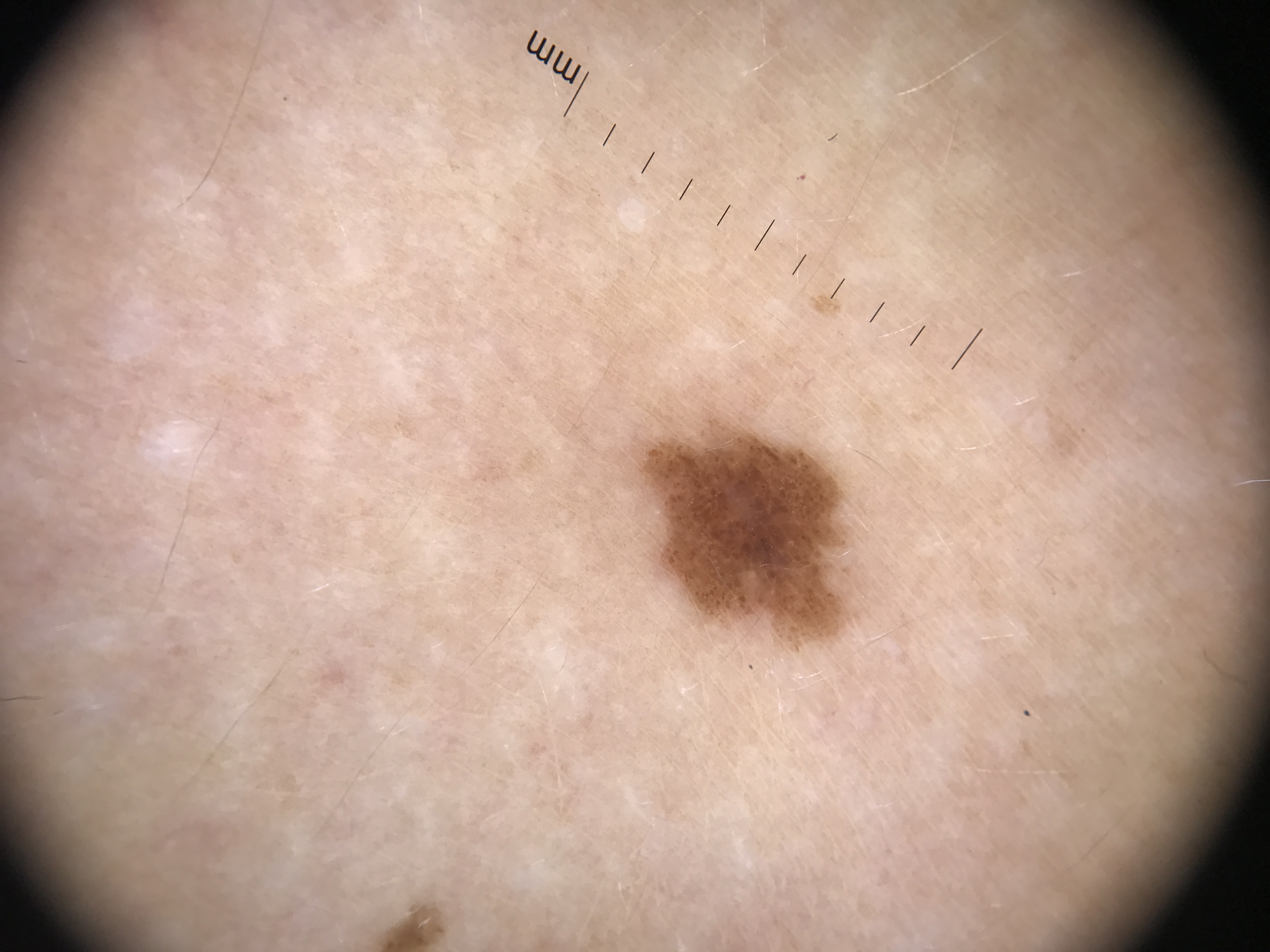class = dysplastic junctional nevus (expert consensus).